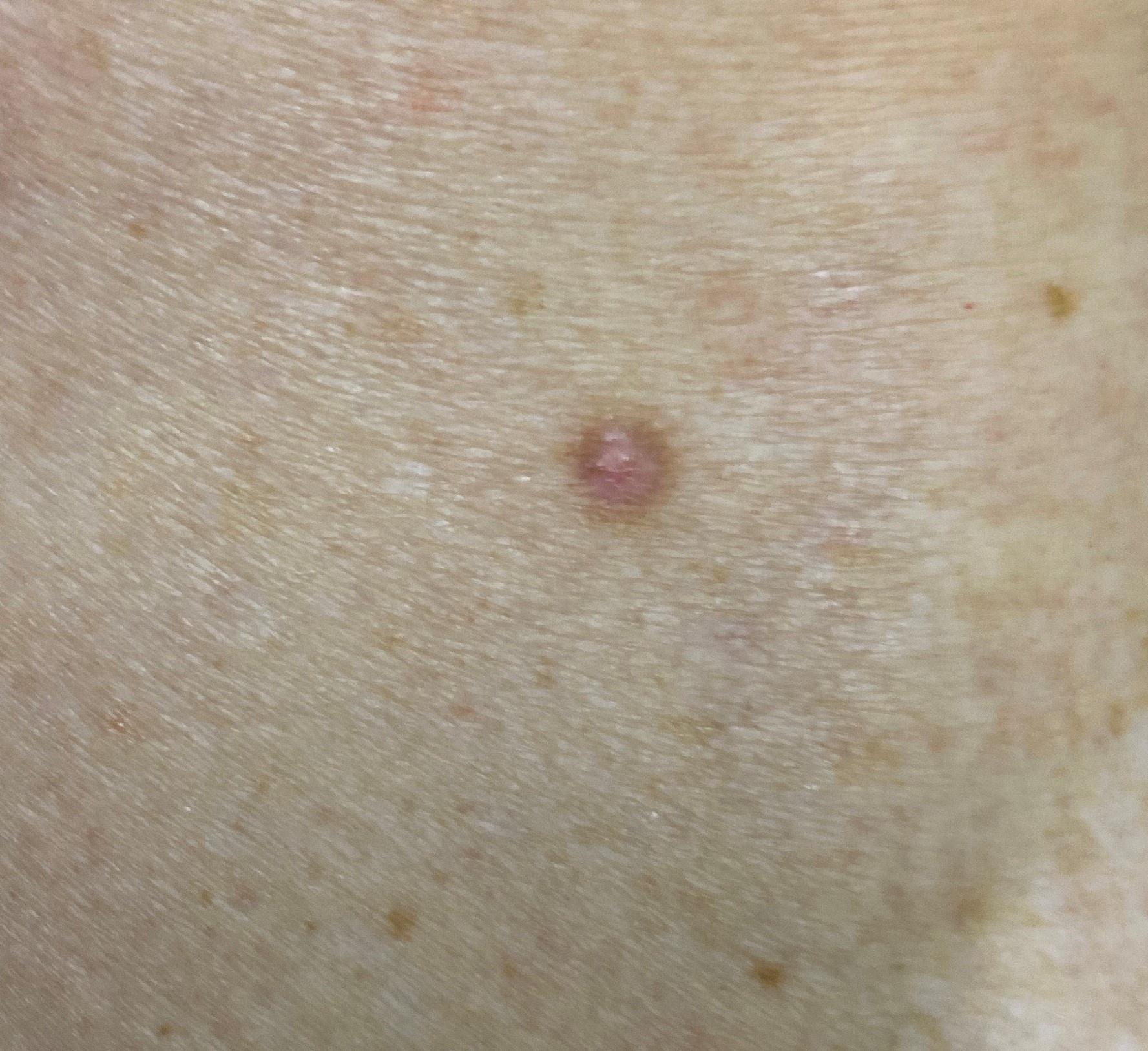A clinical photograph showing a skin lesion in context.
The clinical assessment was a dermatofibroma.